A dermoscopy image of a single skin lesion: 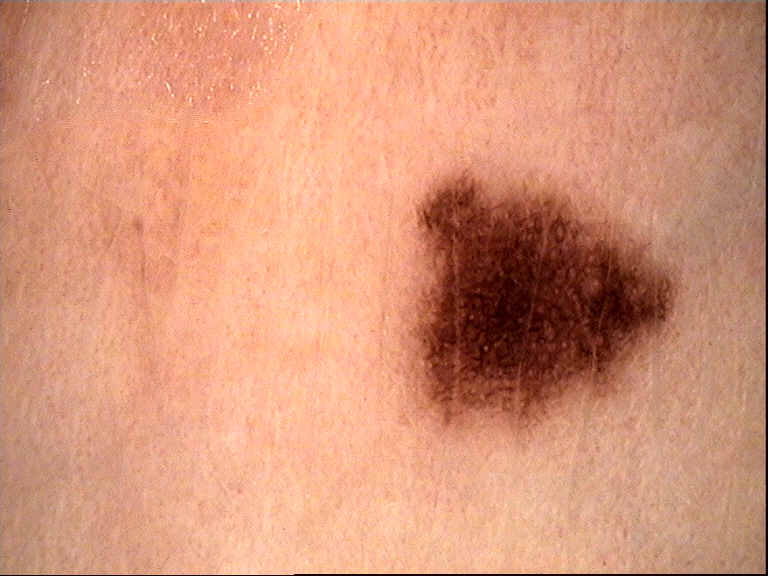Classified as a dysplastic junctional nevus.